Female patient, age 70–79. The lesion involves the top or side of the foot, sole of the foot and palm. Close-up view.
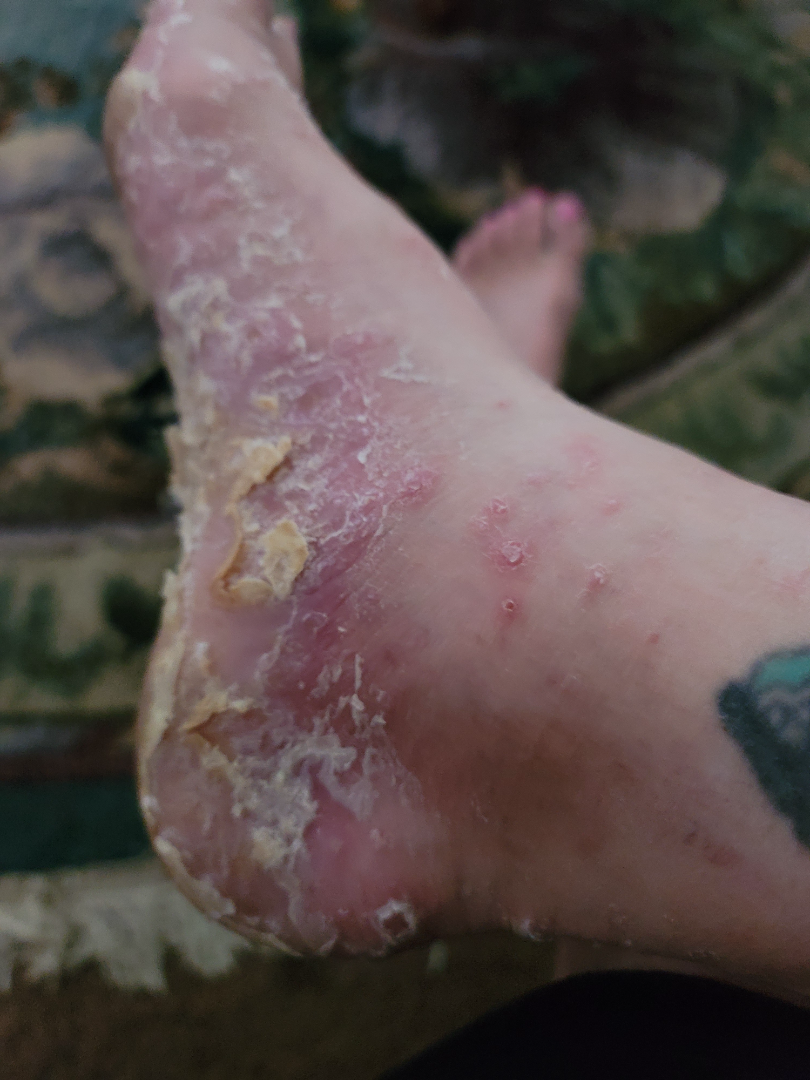The condition could not be reliably identified from the image.
The contributor notes the condition has been present for one to three months.
Reported lesion symptoms include enlargement, itching, burning, bothersome appearance and pain.
Self-categorized by the patient as a rash.
Fitzpatrick II; non-clinician graders estimated Monk Skin Tone 1 (US pool) or 2 (India pool).
The contributor notes the lesion is rough or flaky.
The patient also reports fatigue and shortness of breath.